The photo was captured at an angle: 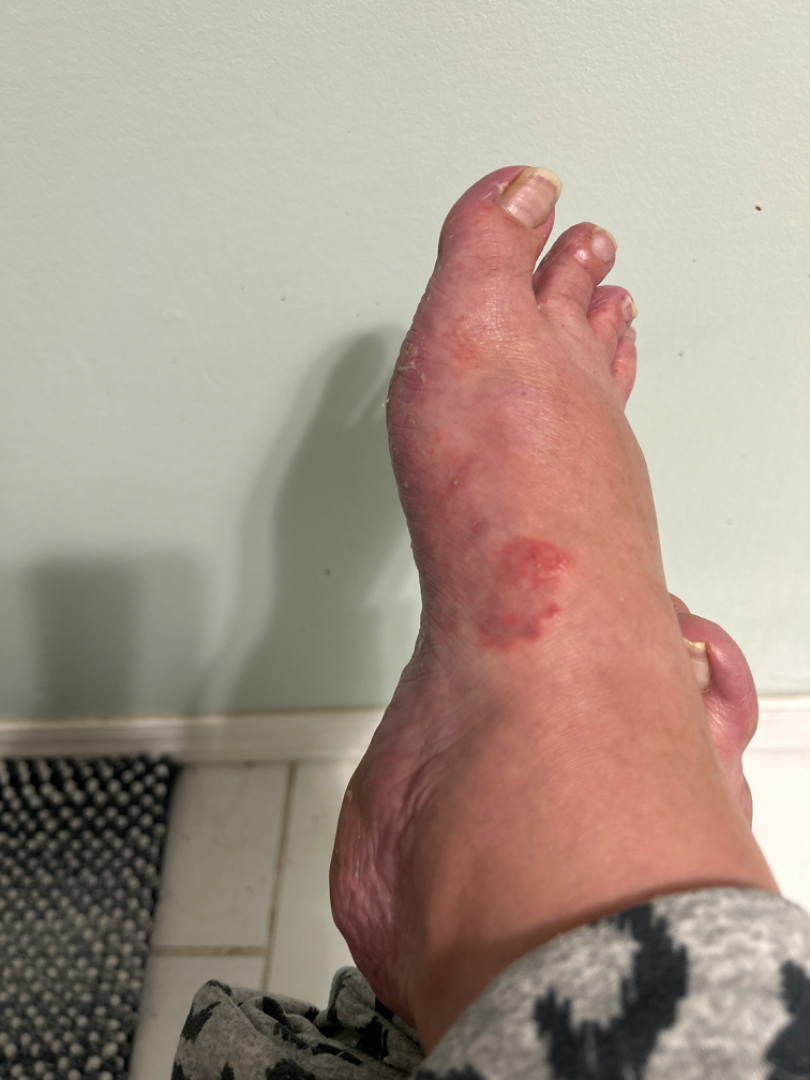Case summary:
- differential diagnosis — one reviewing dermatologist: the impression on review was Granuloma annulare